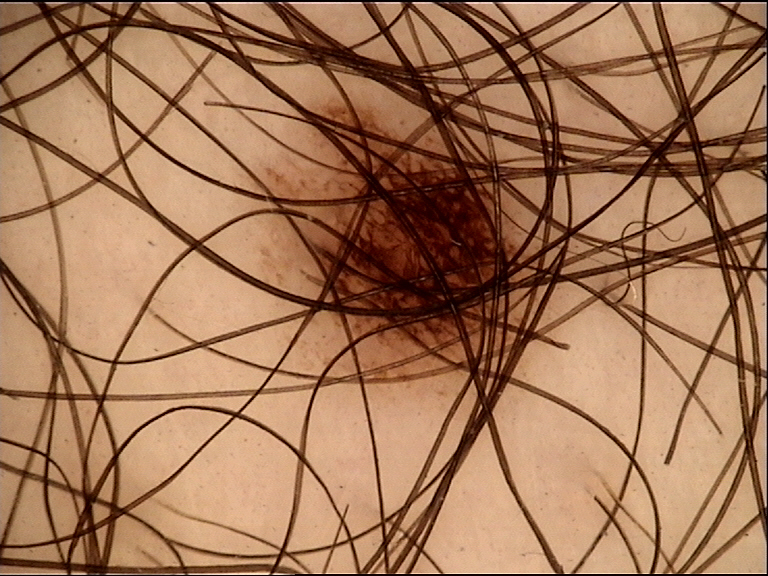The diagnostic label was a dysplastic junctional nevus.